Dermoscopy of a skin lesion.
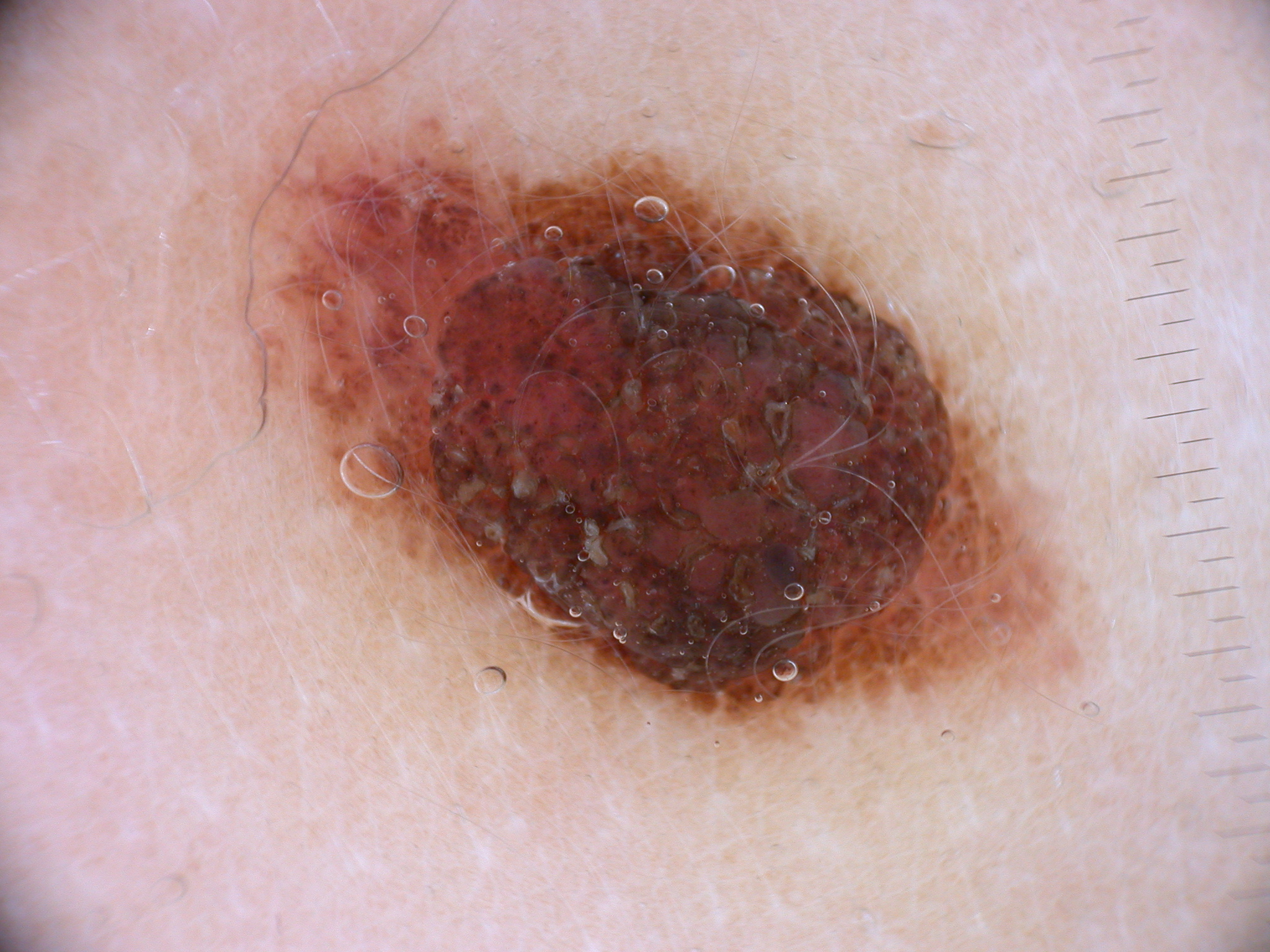On dermoscopy, the lesion shows pigment network, with no streaks, negative network, globules, or milia-like cysts. The lesion takes up about 24% of the image. The lesion occupies the region 273 120 1044 722. The lesion was assessed as a melanocytic nevus, a benign lesion.